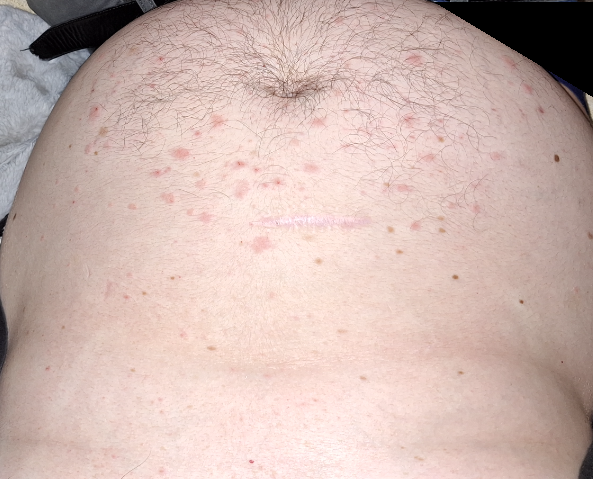Notes:
• framing — at a distance
• clinical impression — the differential is split between Pityriasis lichenoides, Scabies and Folliculitis